The affected area is the leg; male subject, age 18–29; a close-up photograph — 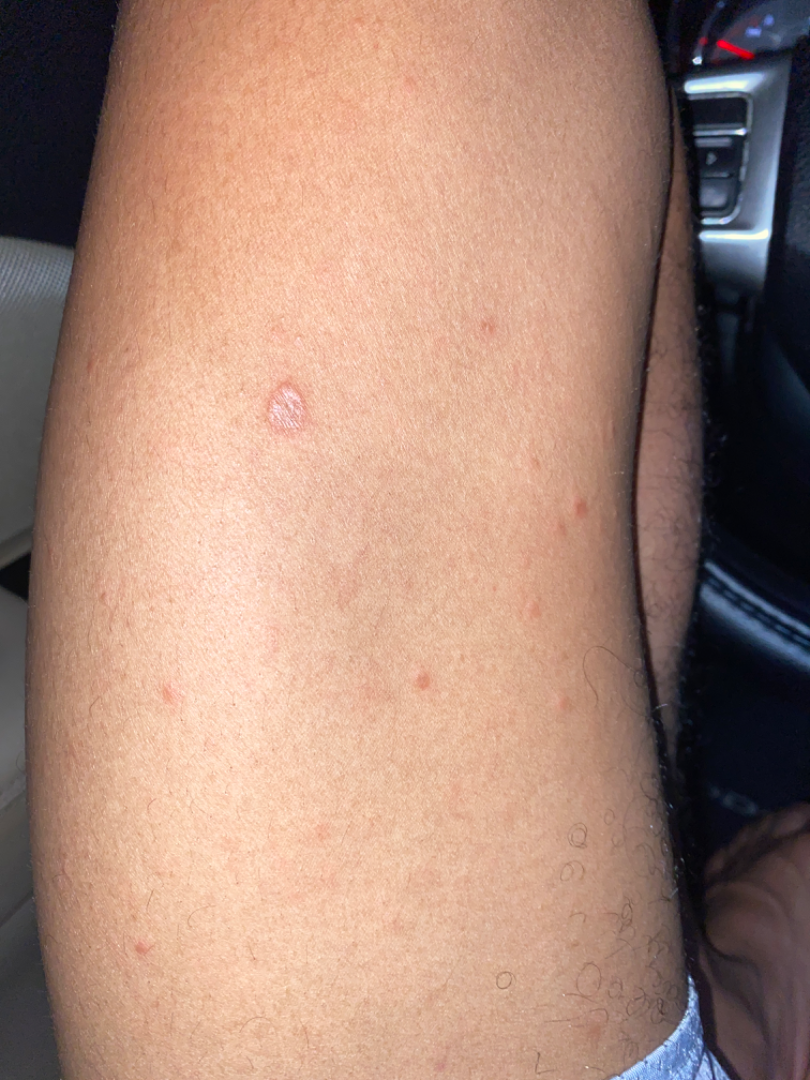Patient information:
The condition has been present for one to four weeks. The patient described the issue as a rash. The lesion is described as raised or bumpy. Reported lesion symptoms include bothersome appearance.
Review:
On photographic review, favoring Psoriasis; also raised was Lichen planus/lichenoid eruption; also consider Syphilis; a remote consideration is Drug Rash; less probable is Eczema.